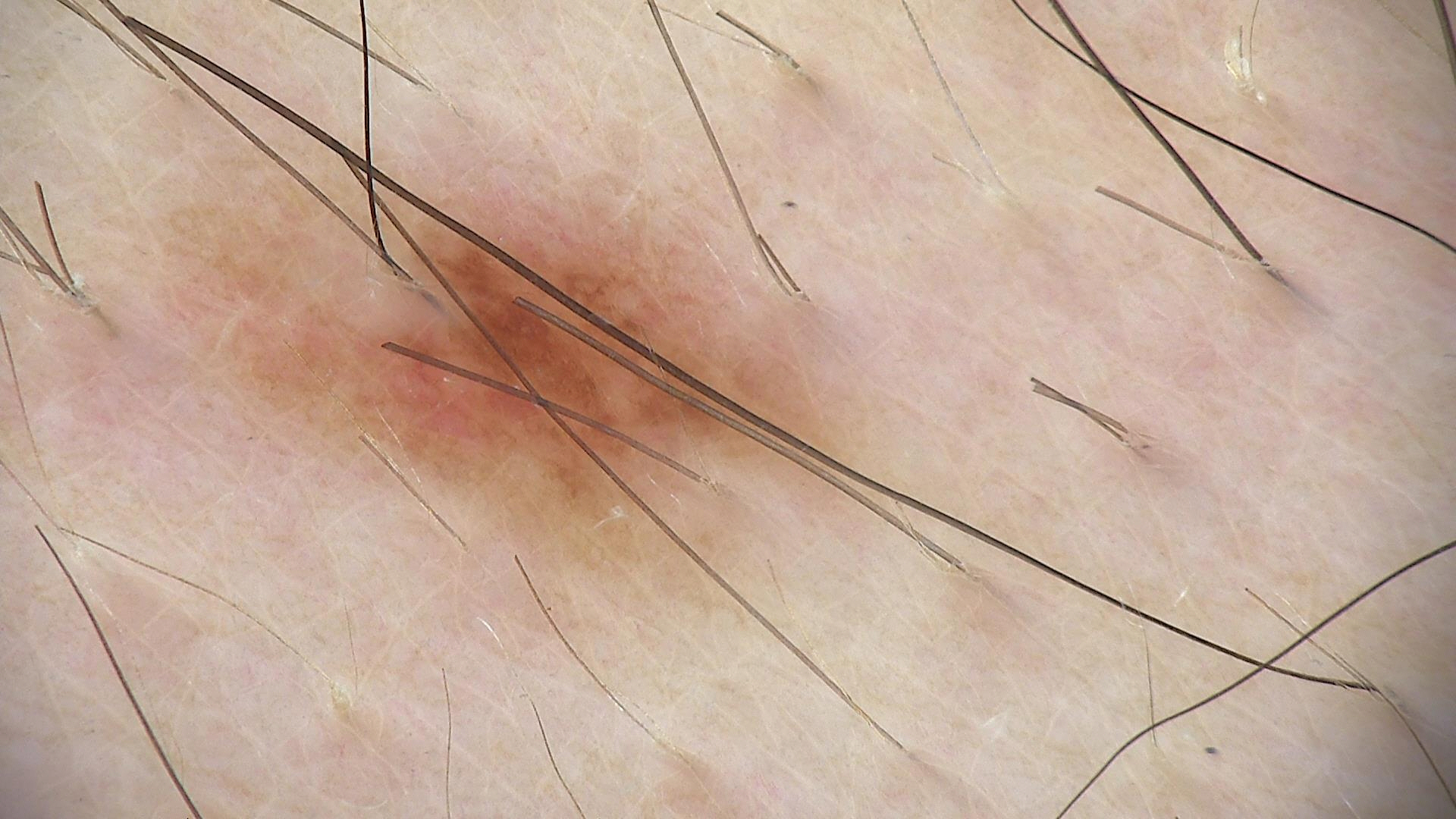  image: dermoscopy
  diagnosis:
    name: dysplastic junctional nevus
    code: jd
    malignancy: benign
    super_class: melanocytic
    confirmation: expert consensus